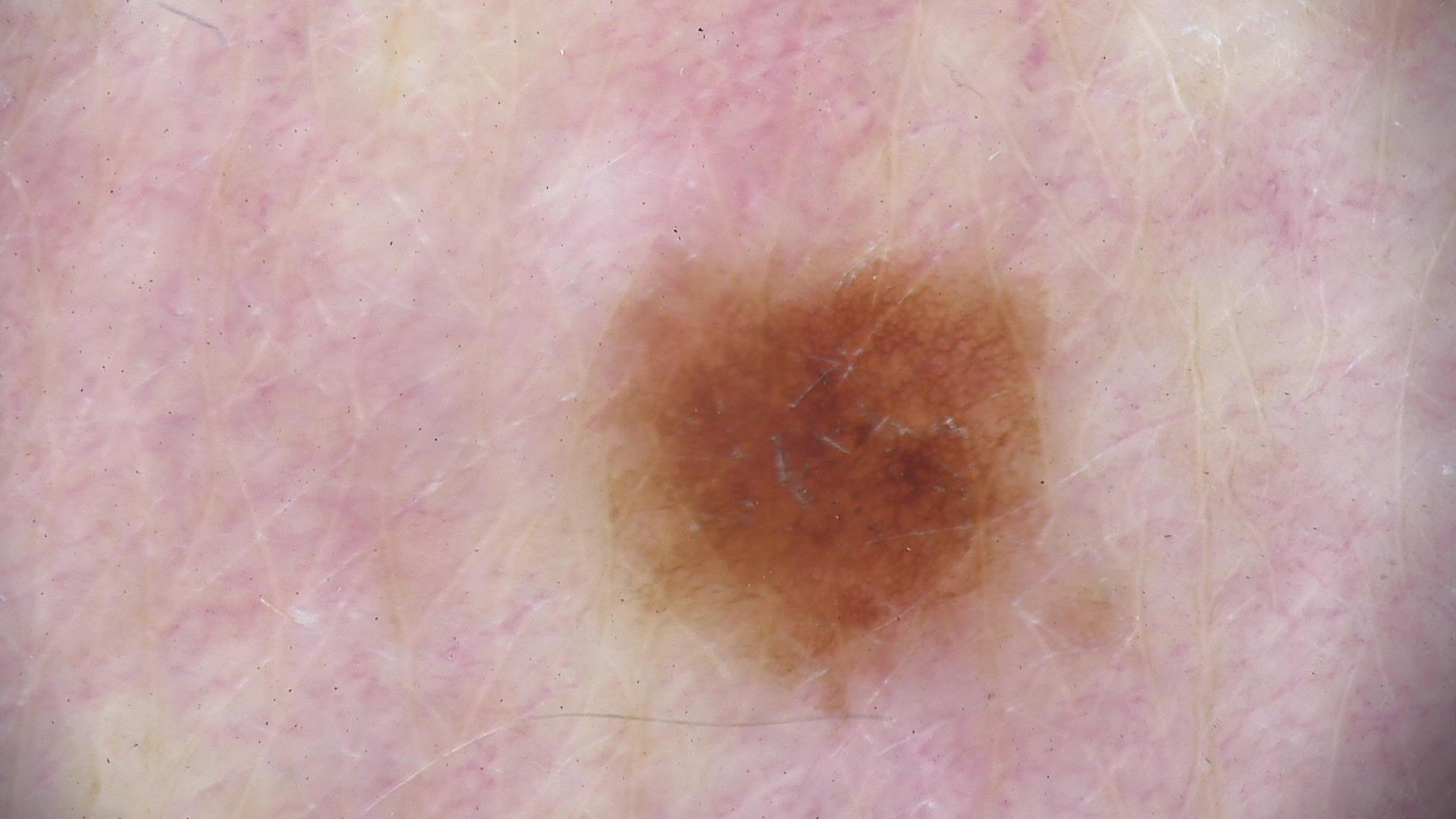Classified as a dysplastic junctional nevus.